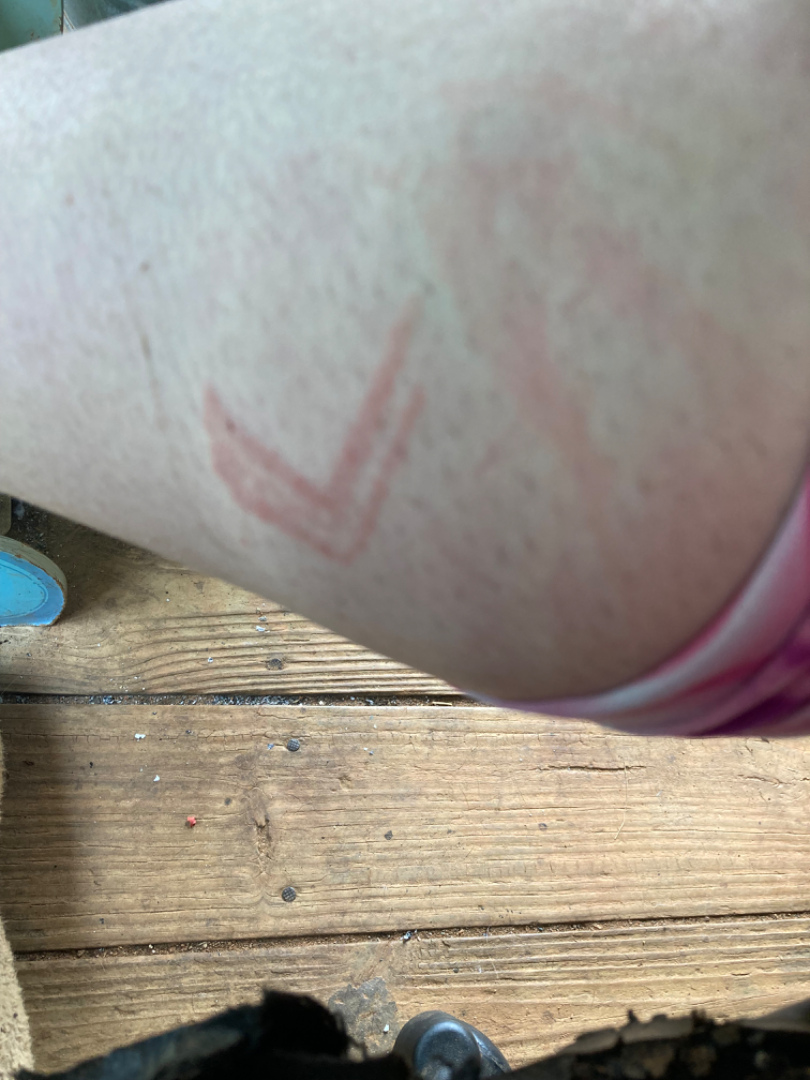History:
An image taken at a distance.
Impression:
On photographic review, Burn of skin and Allergic Contact Dermatitis were each considered, in no particular order.